A dermoscopic image of a skin lesion · a male subject 89 years old — 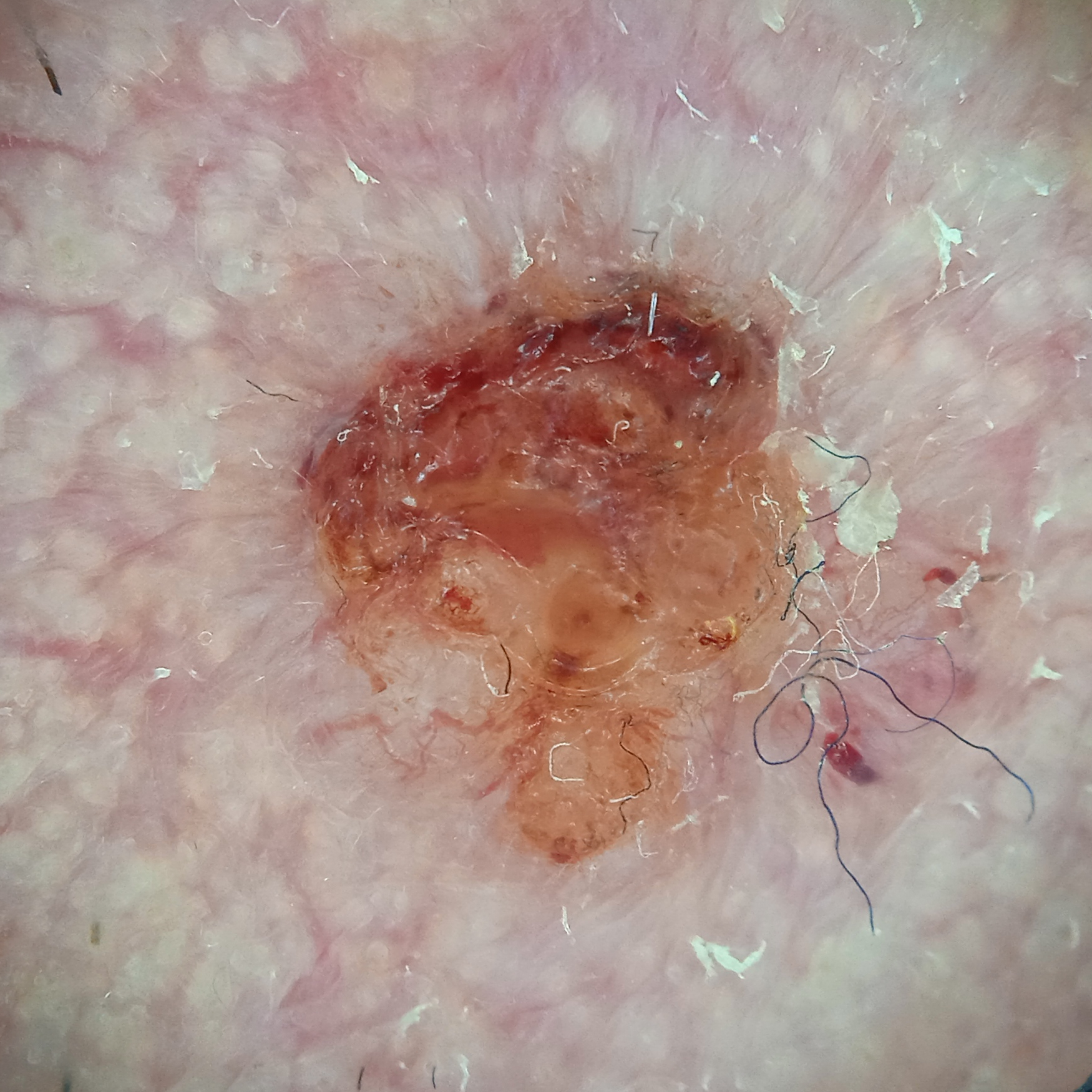site: the face
size: 8.5 mm
pathology: basal cell carcinoma (biopsy-proven)